The condition has been present for about one day · the lesion is described as raised or bumpy · the contributor is 50–59, female · the photograph is a close-up of the affected area · the affected area is the back of the torso, front of the torso and leg.
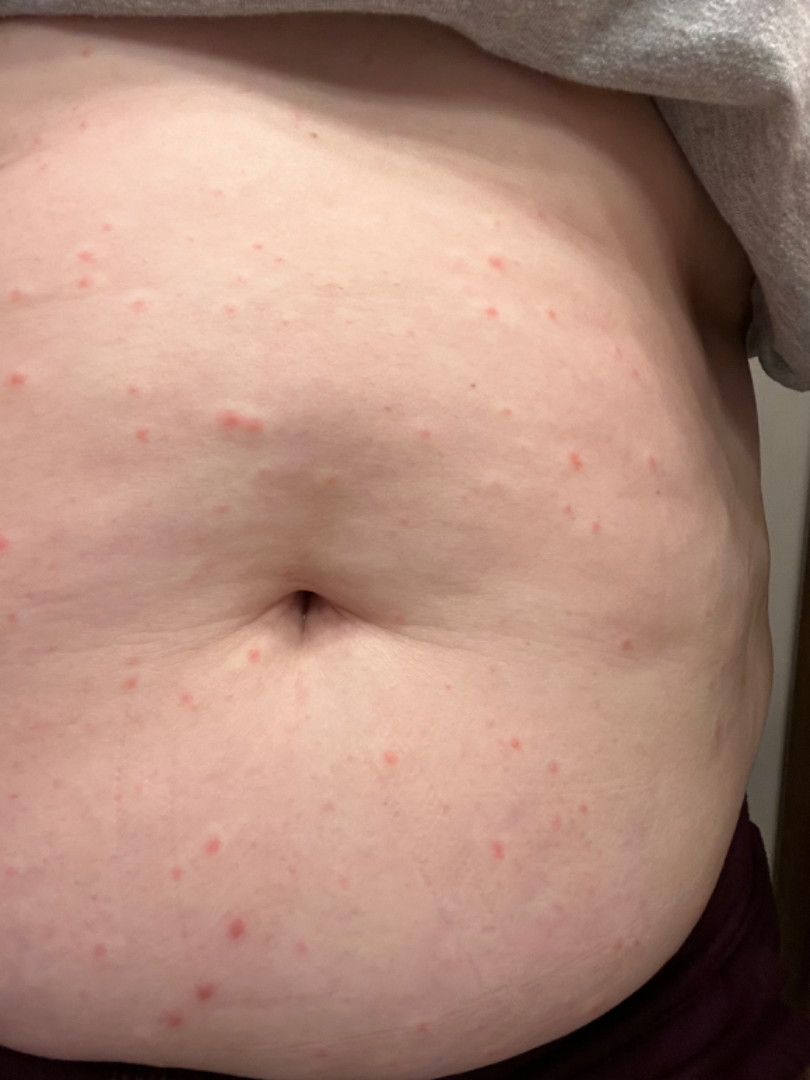| field | value |
|---|---|
| diagnostic considerations | the differential, in no particular order, includes Scabies, Folliculitis and Insect Bite |